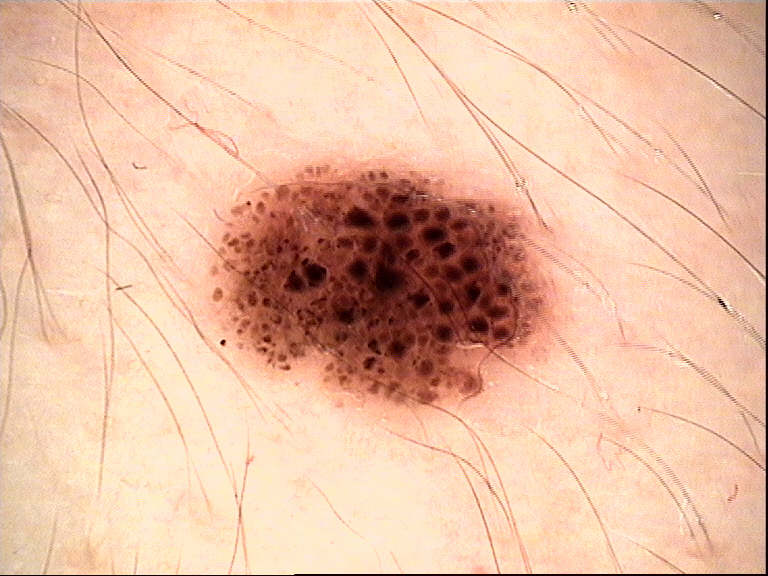subtype=banal | label=compound nevus (expert consensus).